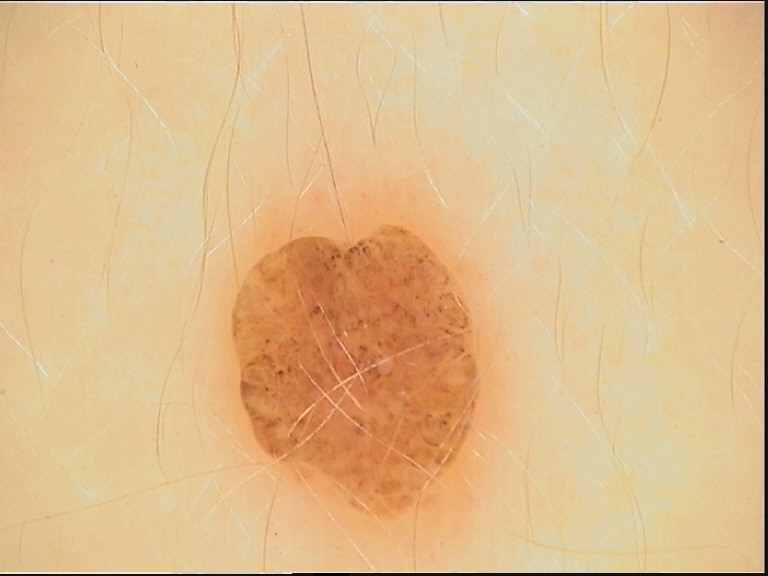Case:
• imaging — dermatoscopy
• lesion type — banal
• class — dermal nevus (expert consensus)